A skin lesion imaged with a dermatoscope.
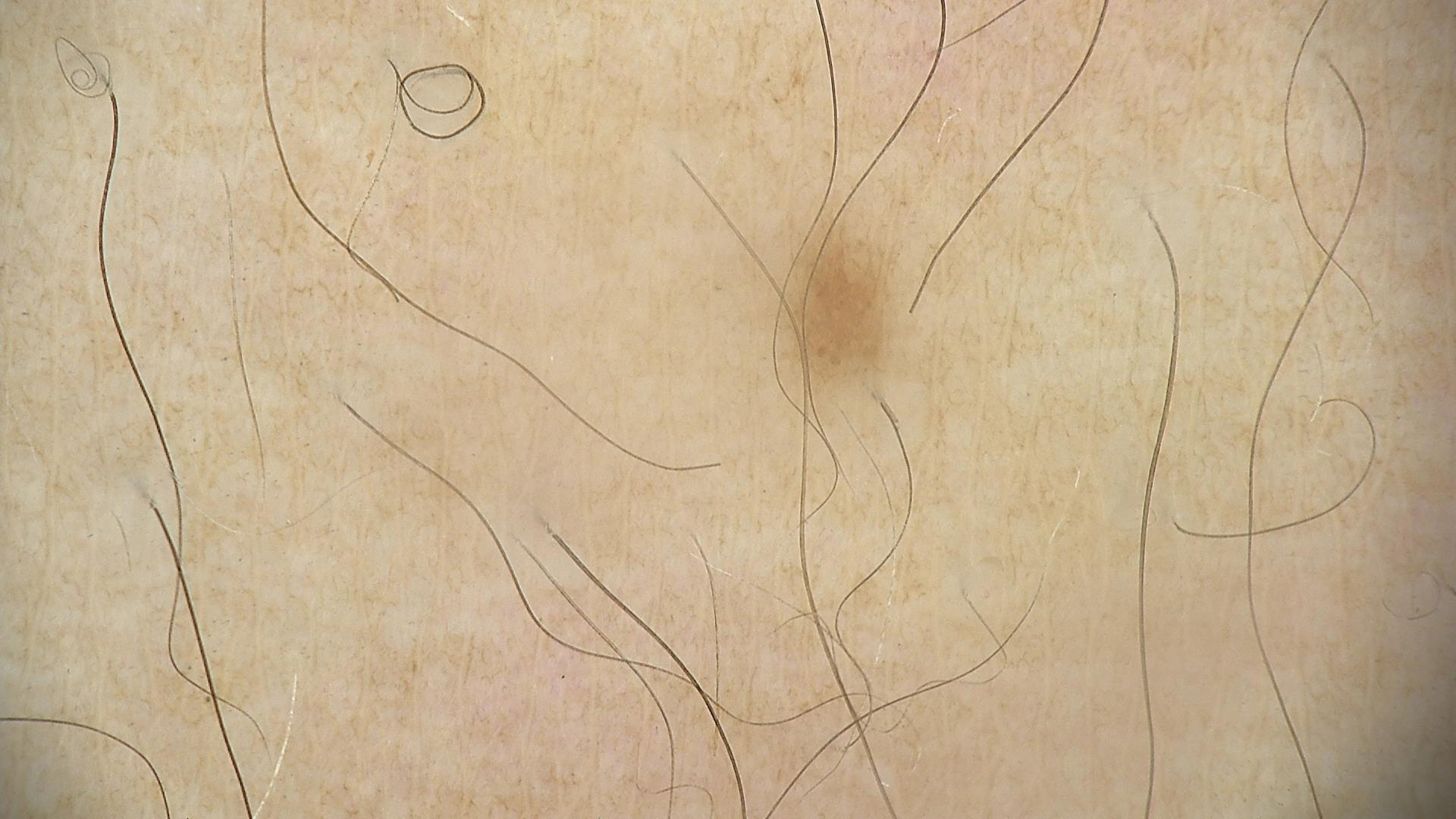Conclusion: Labeled as a dysplastic junctional nevus.